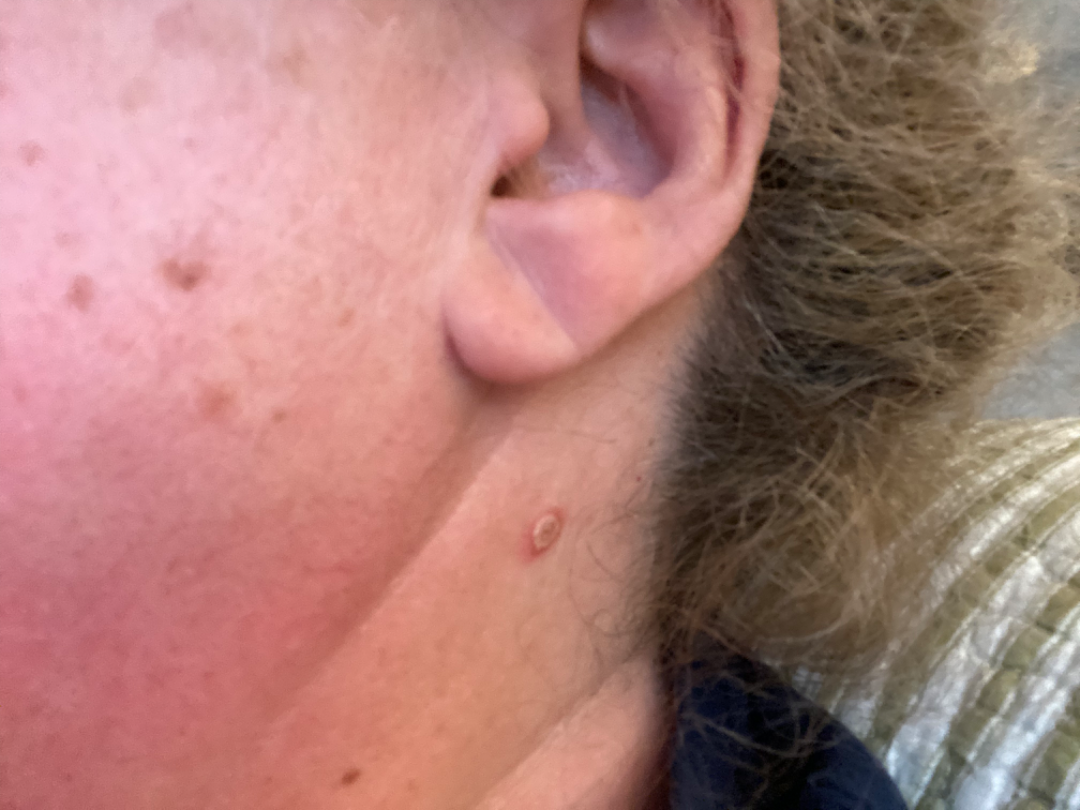Impression:
The skin condition could not be confidently assessed from this image.
History:
An image taken at a distance.